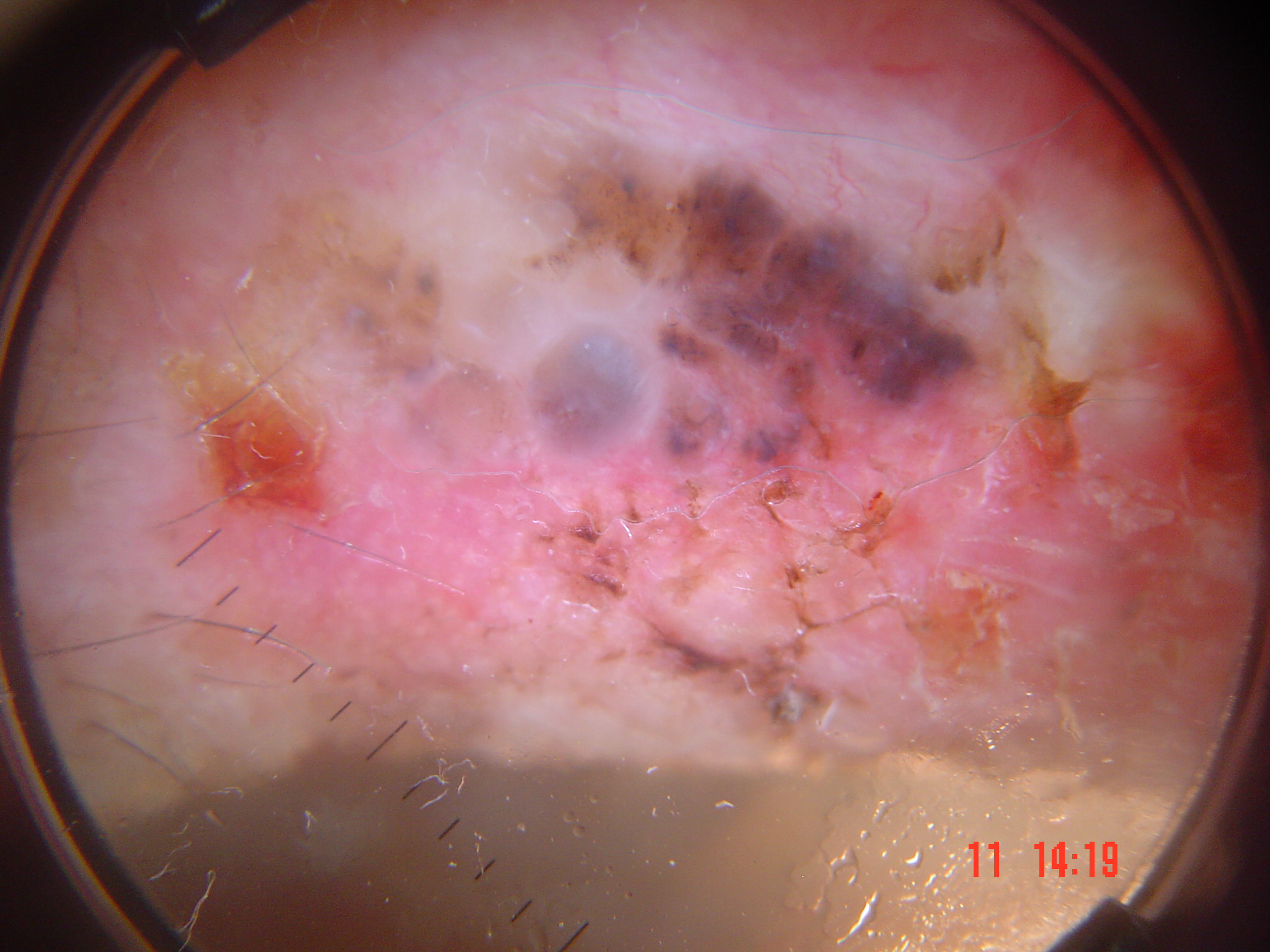Conclusion:
The biopsy diagnosis was a skin cancer — a basal cell carcinoma.